A female subject 48 years old. The patient says their skin reddens painfully with sun exposure. Acquired for a research image collection, with no referral diagnosis. Few moles overall by the patient's own estimate: 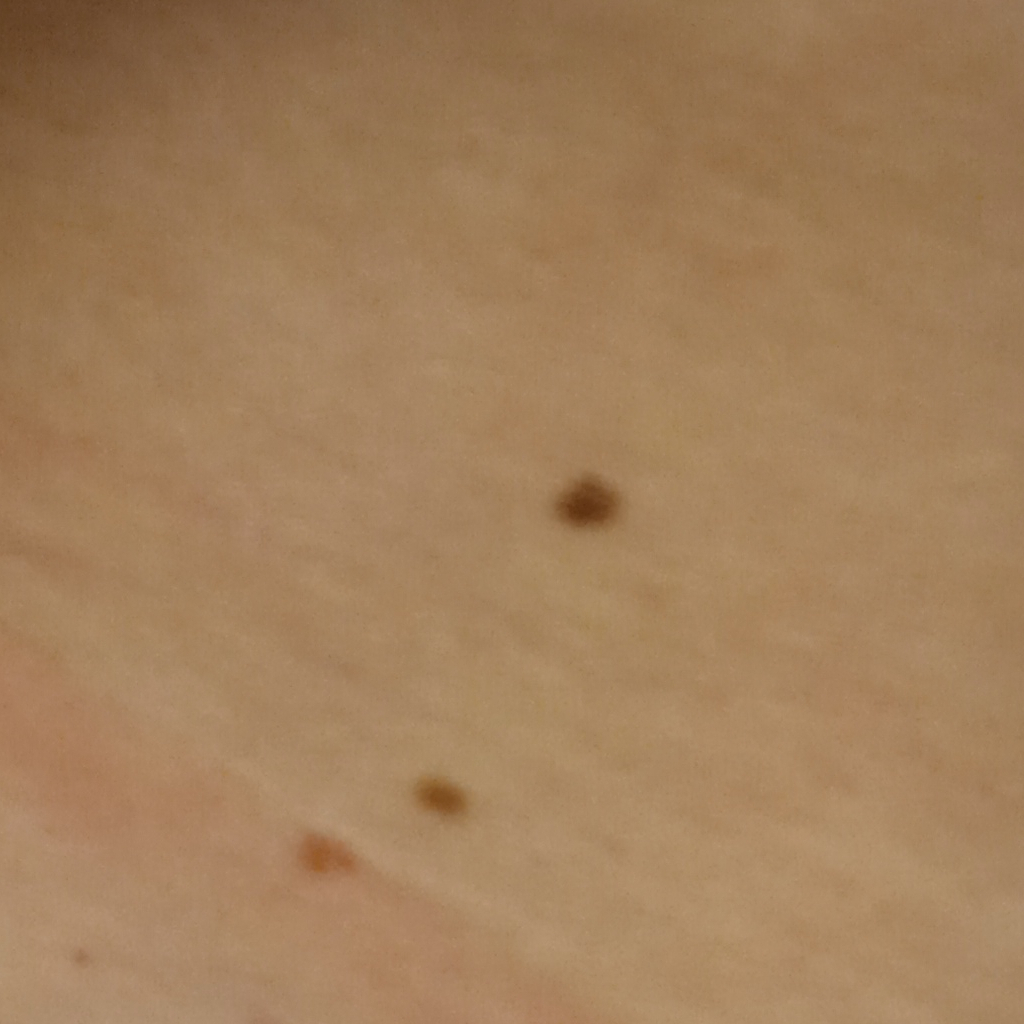Impression:
Dermatologist review favored a melanocytic nevus.